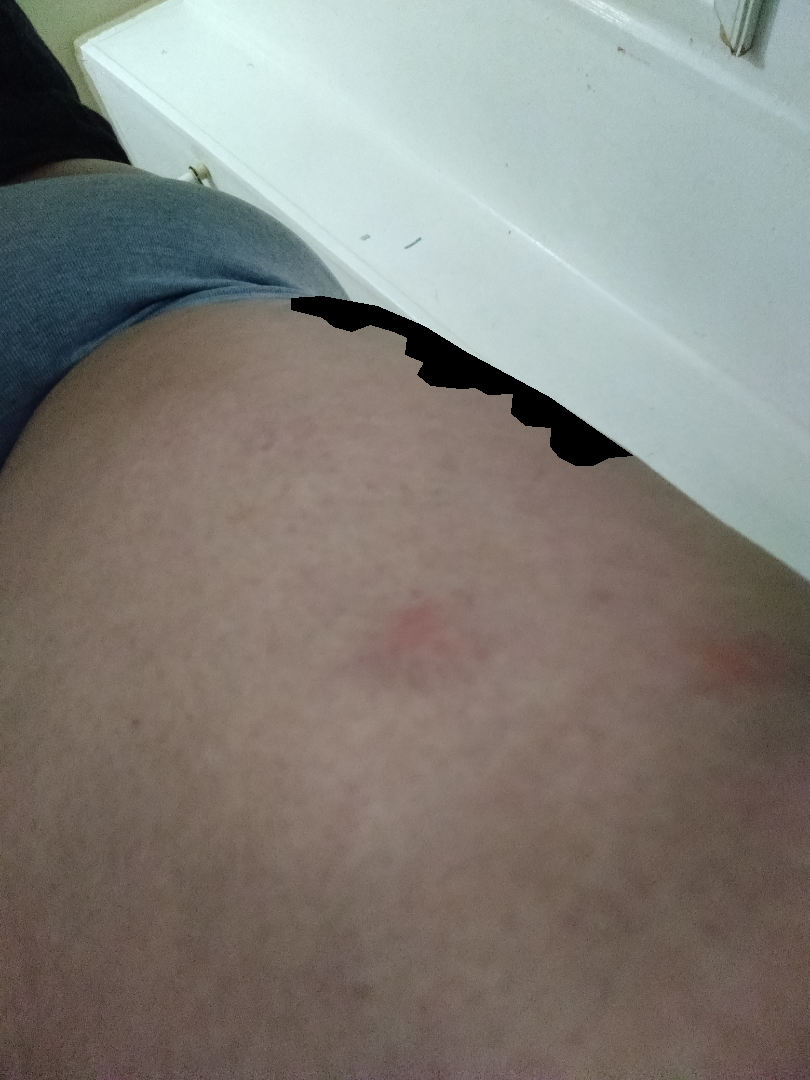Diagnostic features were not clearly distinguishable in this photograph.